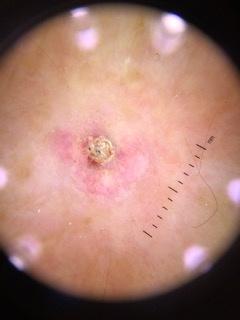| feature | finding |
|---|---|
| diagnostic label | Squamous cell carcinoma (biopsy-proven) |